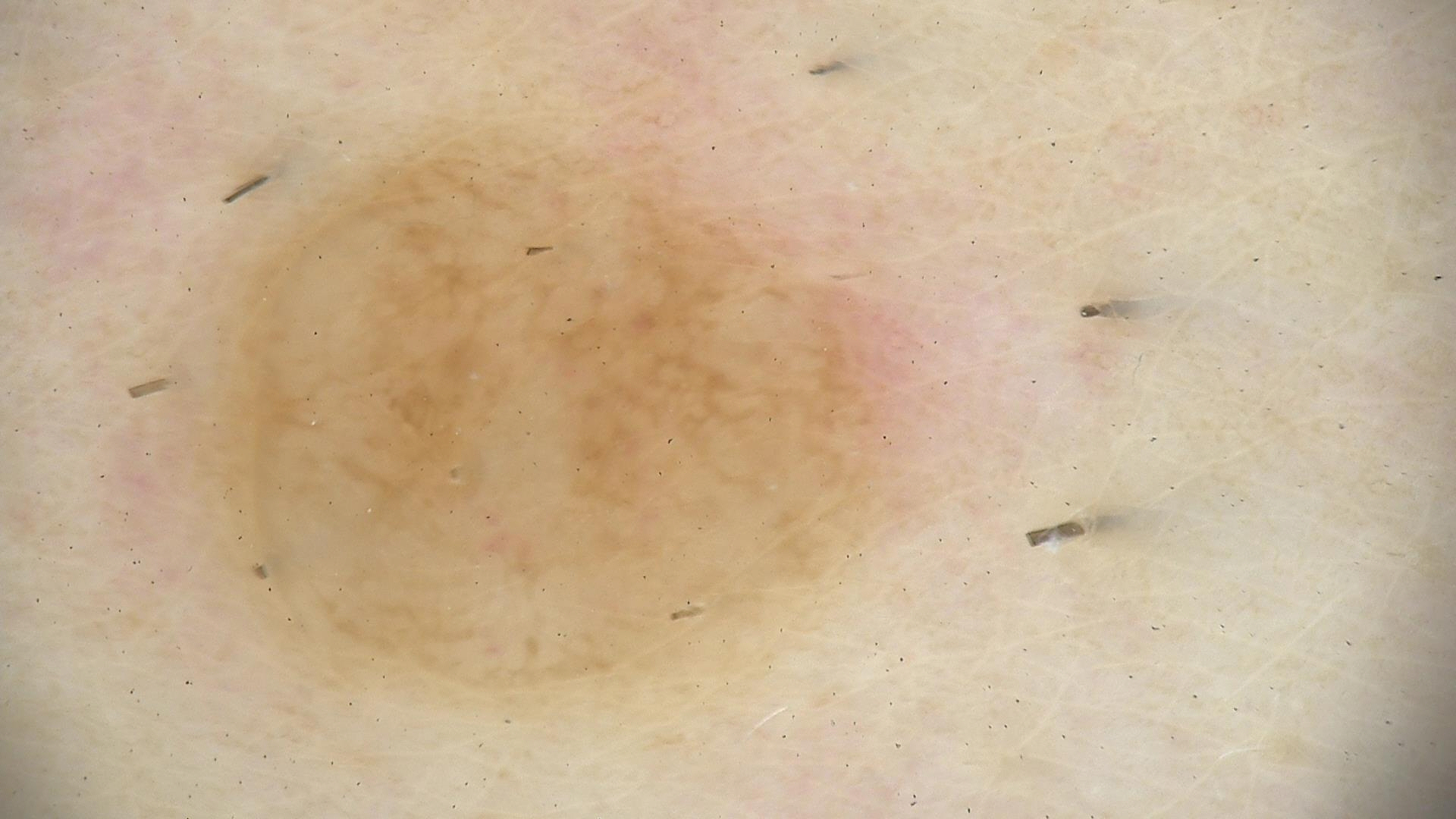image type = dermatoscopy, lesion type = banal, diagnostic label = dermal nevus (expert consensus).